Close-up view:
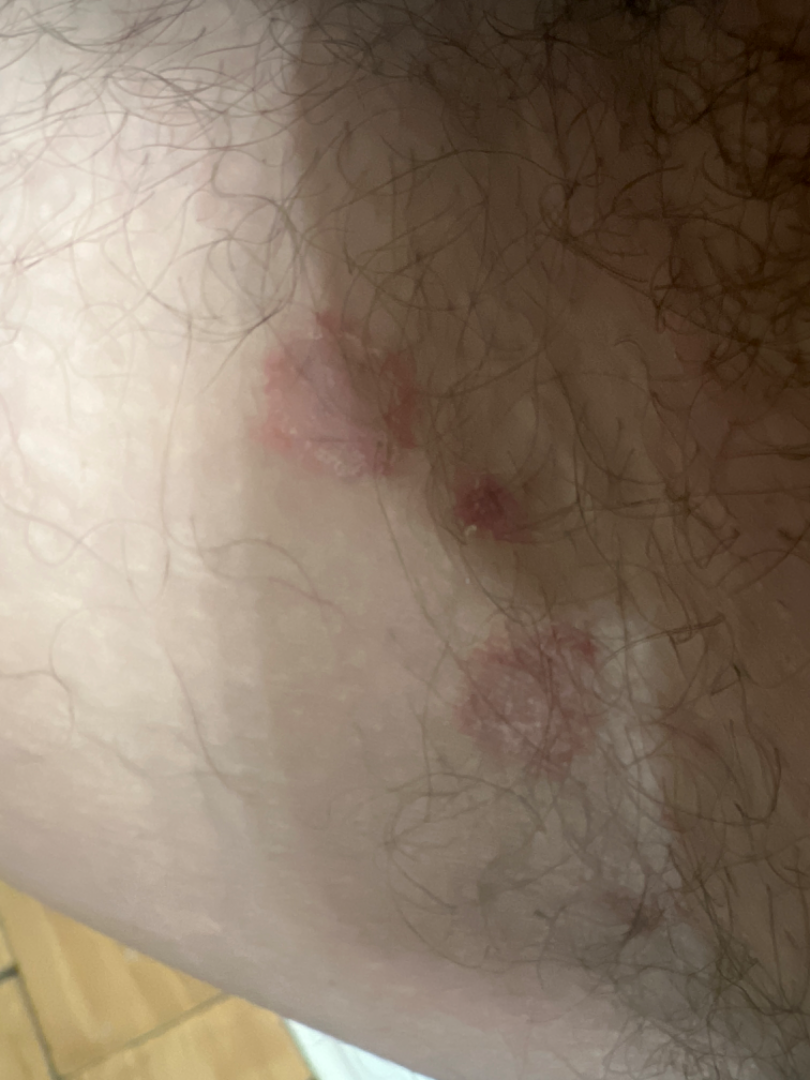assessment — ungradable on photographic review.